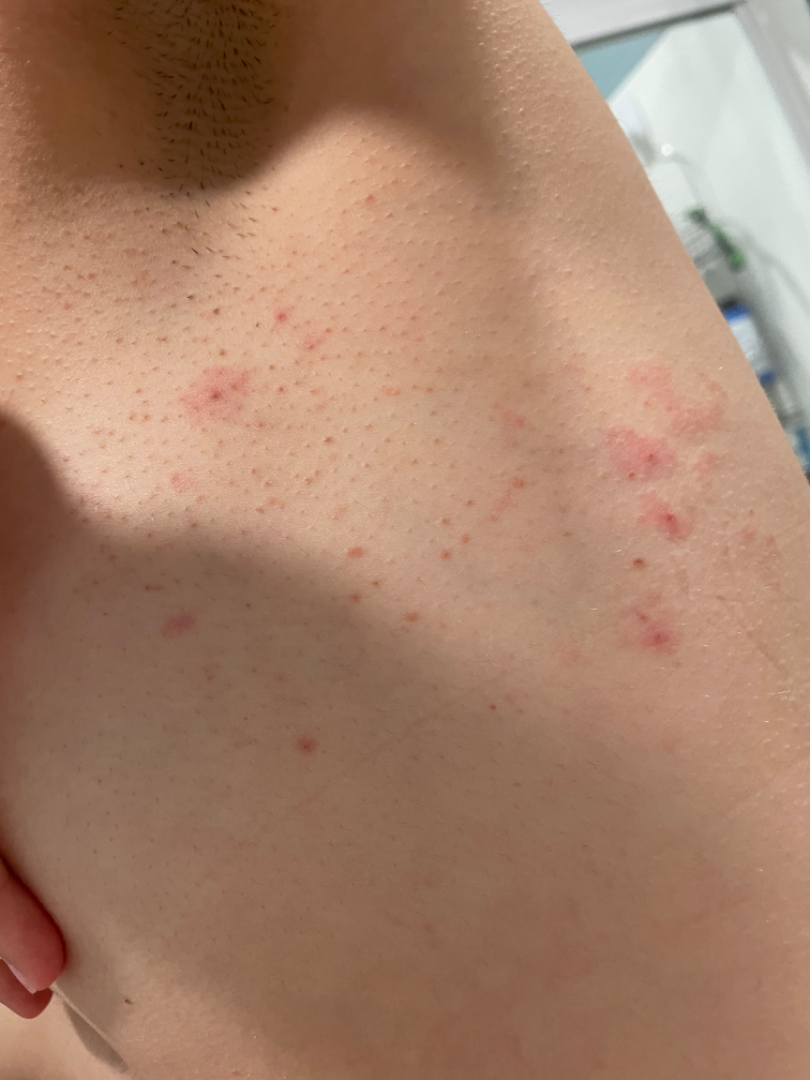No differential diagnosis could be assigned on photographic review.
Female subject, age 18–29.
Close-up view.
Reported lesion symptoms include itching, enlargement and burning.